Dermoscopy of a skin lesion · a female subject, aged approximately 50 — 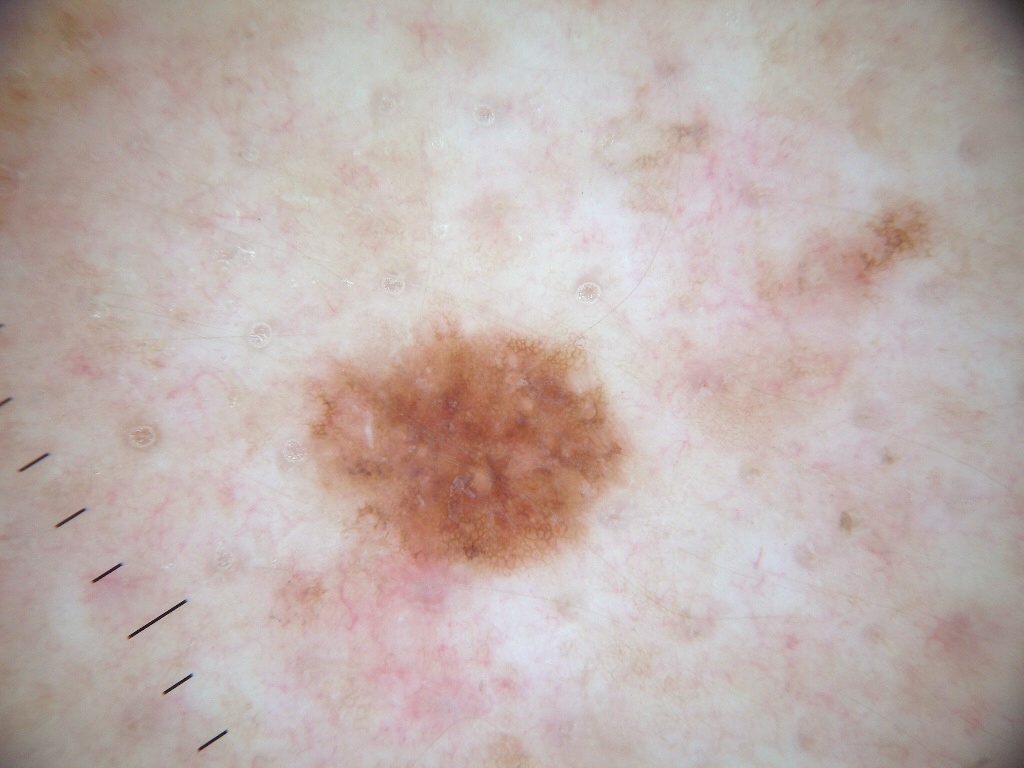<dermoscopy>
<lesion_location>
  <bbox_xyxy>289, 310, 649, 595</bbox_xyxy>
</lesion_location>
<dermoscopic_features>
  <present>pigment network</present>
  <absent>negative network, streaks, milia-like cysts, globules</absent>
</dermoscopic_features>
<diagnosis>
  <name>melanocytic nevus</name>
  <malignancy>benign</malignancy>
  <lineage>melanocytic</lineage>
  <provenance>clinical</provenance>
</diagnosis>
</dermoscopy>